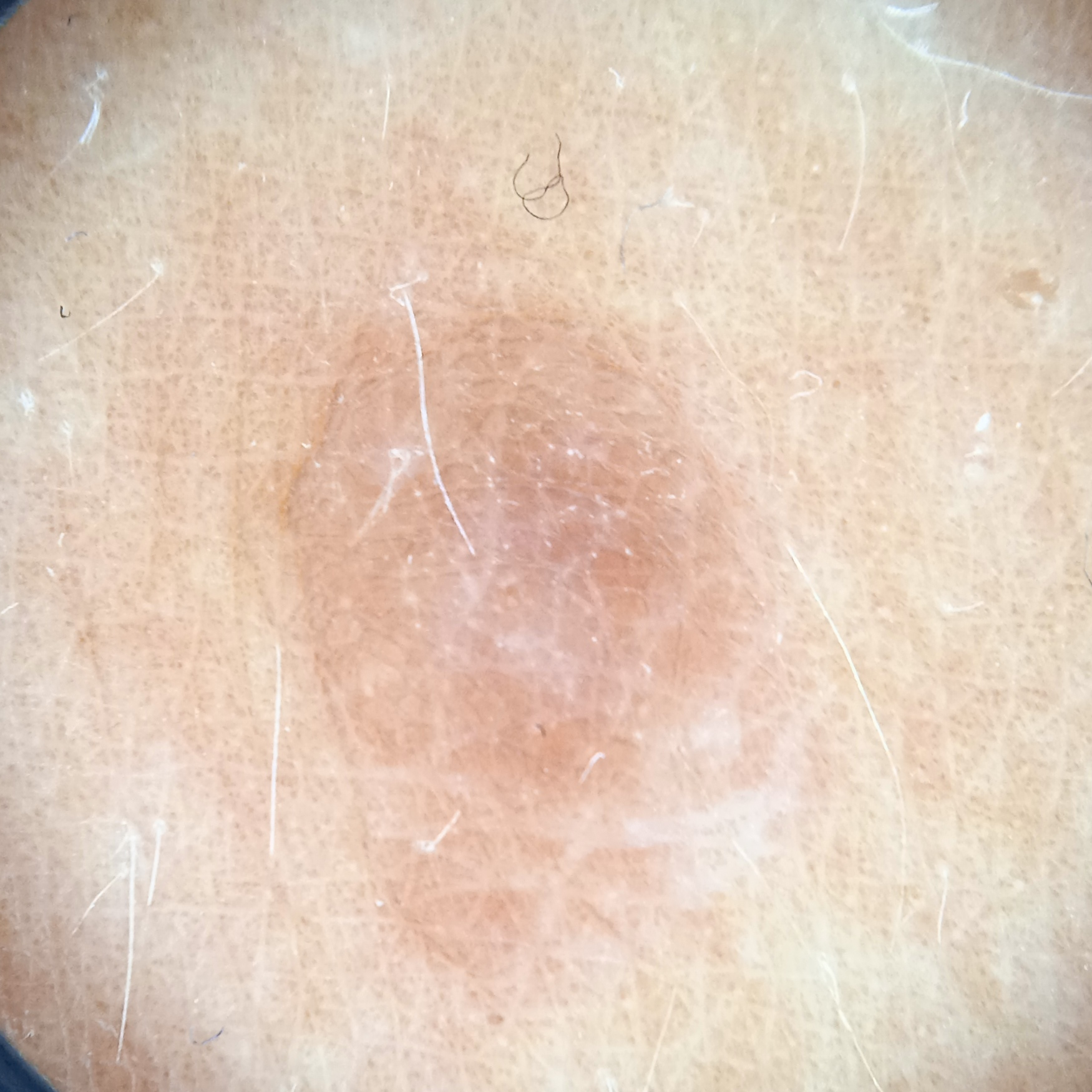A confident diagnosis could not be established from review. Findings: The patient describes having a moderate number of moles. A female subject 47 years of age. The patient reports a history of sunbed use. Collected as part of a research study, without a referral diagnosis. A dermoscopy image of a skin lesion. The patient says their skin tans without first burning. The lesion is located on an arm. The lesion measures approximately 8.1 mm.